A dermoscopy image of a single skin lesion — 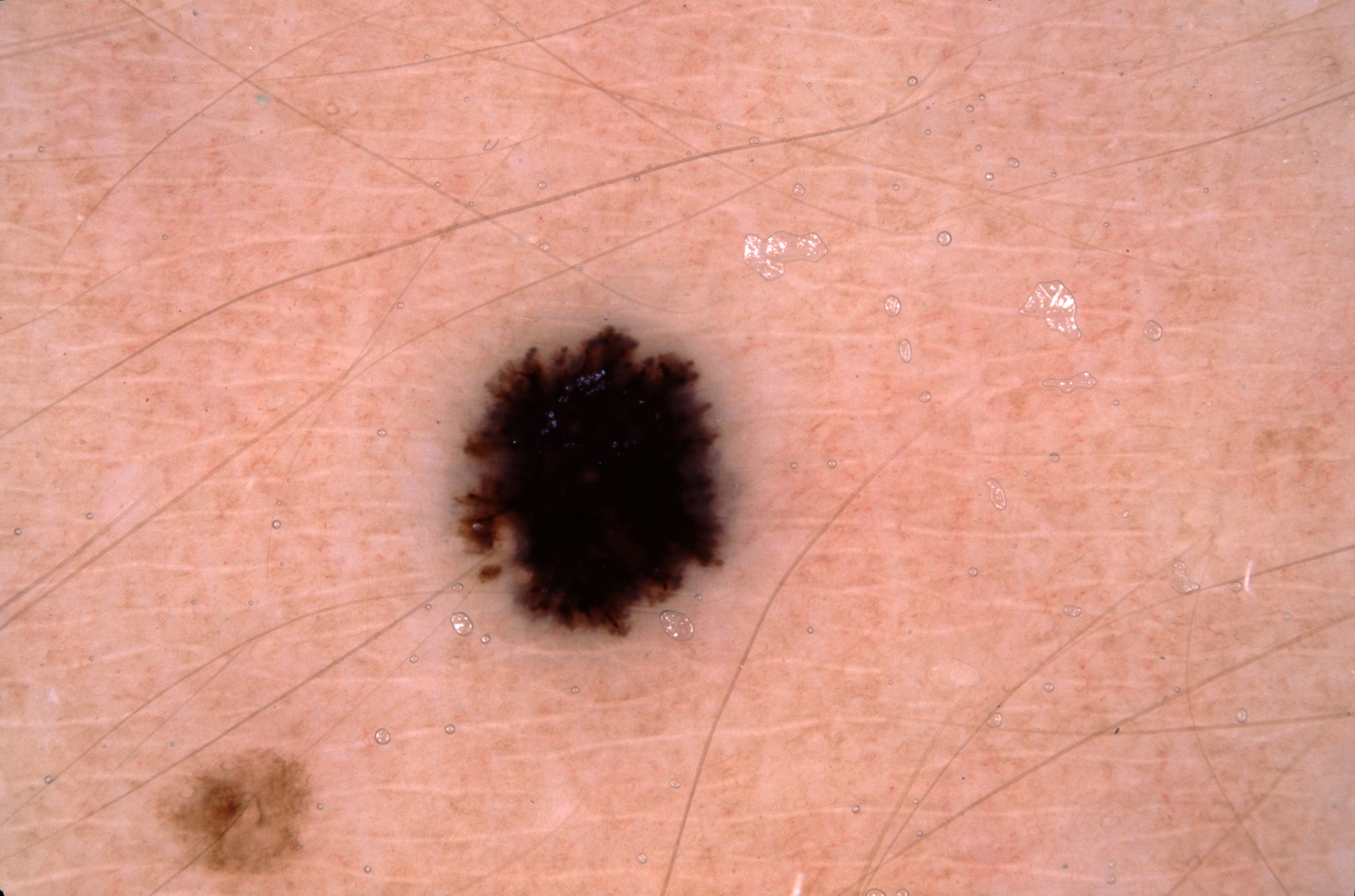Dermoscopic examination shows streaks.
The lesion spans bbox(452, 324, 742, 638).
Clinically diagnosed as a melanocytic nevus.